A female subject 58 years of age; the chart notes tobacco use and pesticide exposure; FST III; a clinical photograph showing a skin lesion — 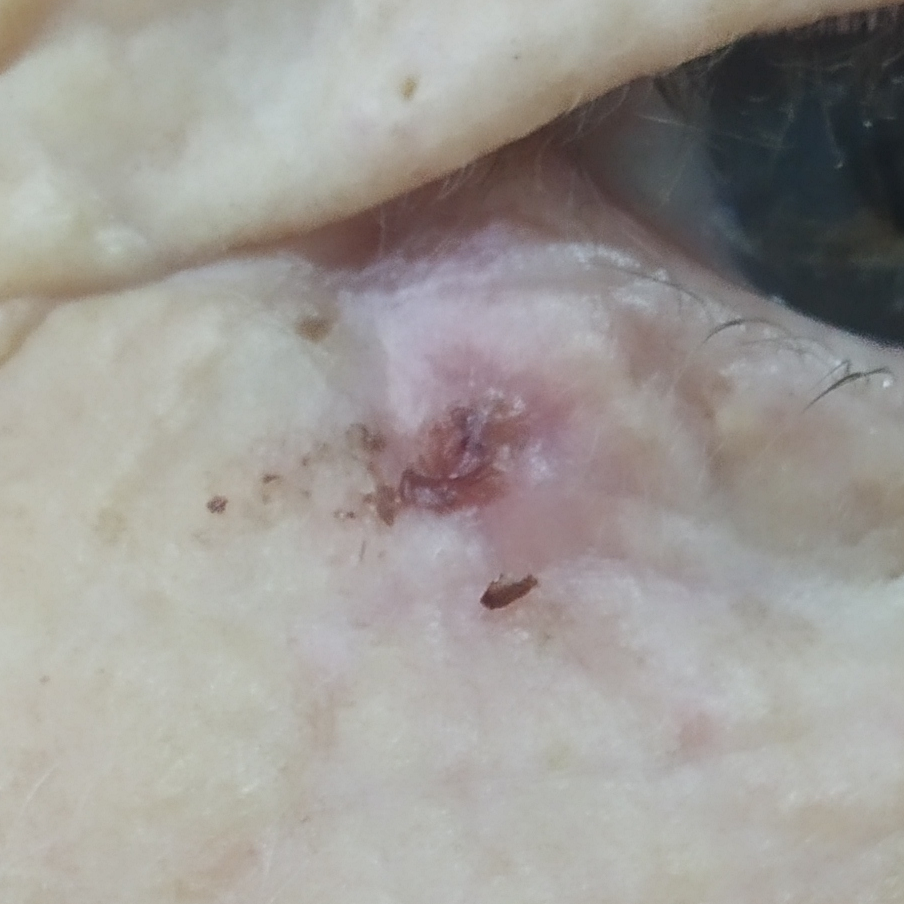The lesion is on the face. Measuring about 4 × 3 mm. The patient describes that the lesion has bled, is elevated, and itches. On biopsy, the diagnosis was a basal cell carcinoma.